A dermatoscopic image of a skin lesion.
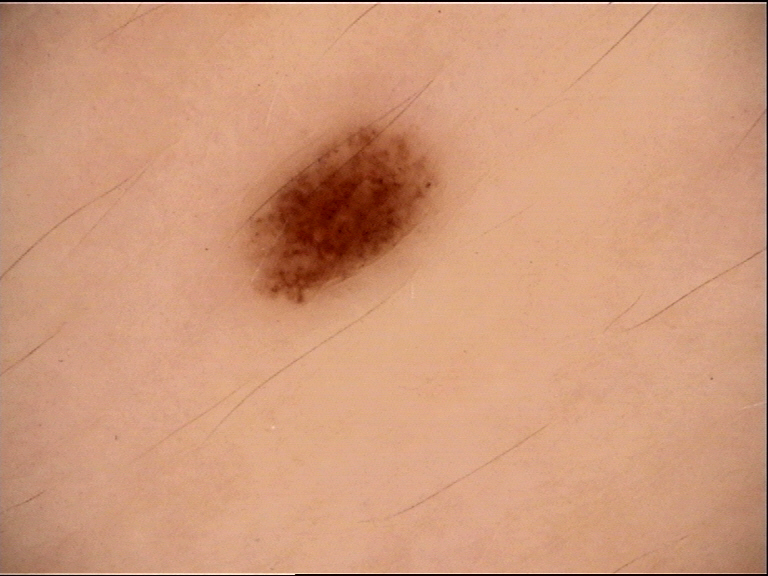label: dysplastic junctional nevus (expert consensus).